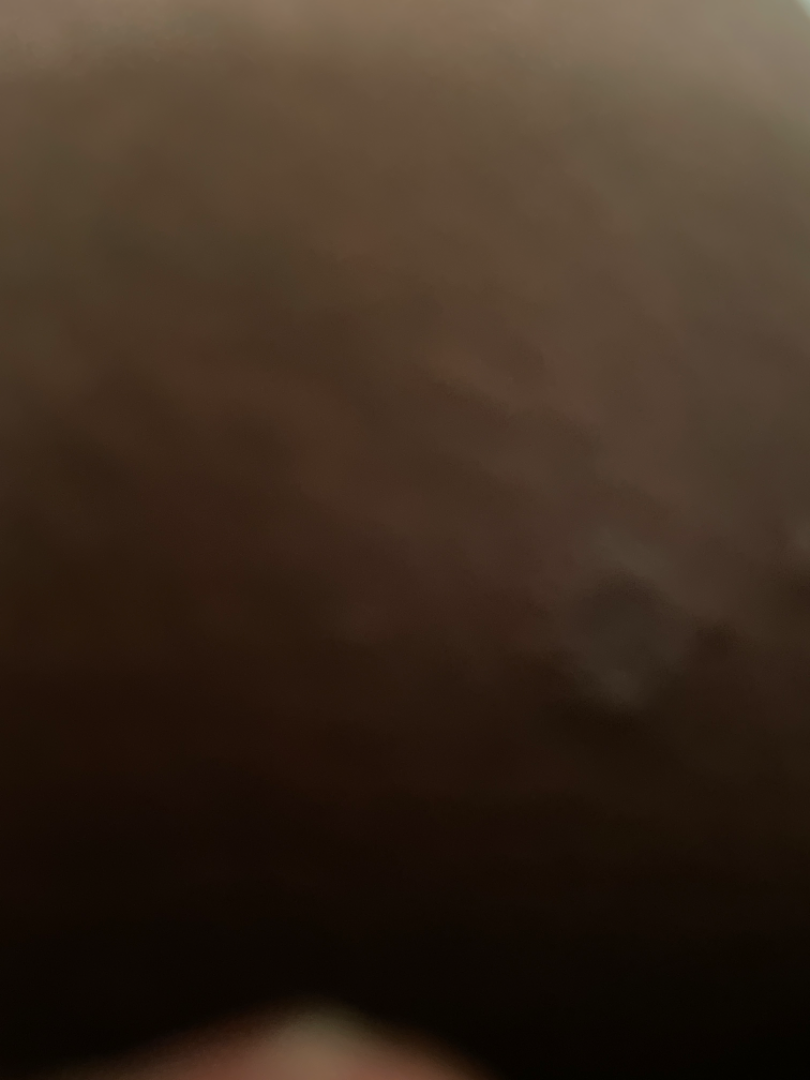Case summary:
– assessment — indeterminate from the photograph